No relevant systemic symptoms · the photo was captured at a distance · the leg is involved · the subject is female · the patient notes bothersome appearance, itching and pain · self-categorized by the patient as a rash · the condition has been present for less than one week.
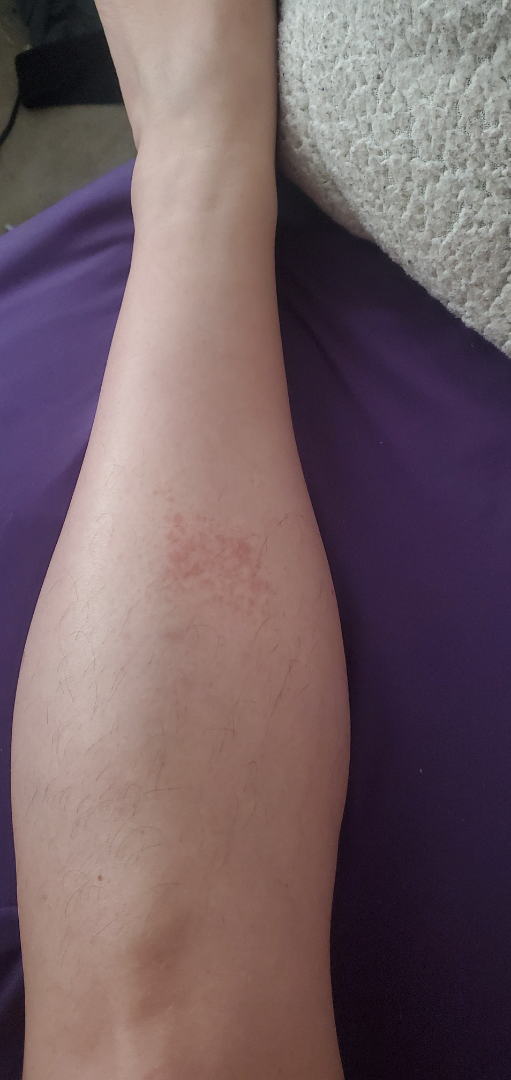diagnostic considerations = the leading impression is Contact dermatitis; lower on the differential is Eczema; less likely is Allergic Contact Dermatitis; less probable is Miliaria; a more distant consideration is Acute dermatitis, NOS